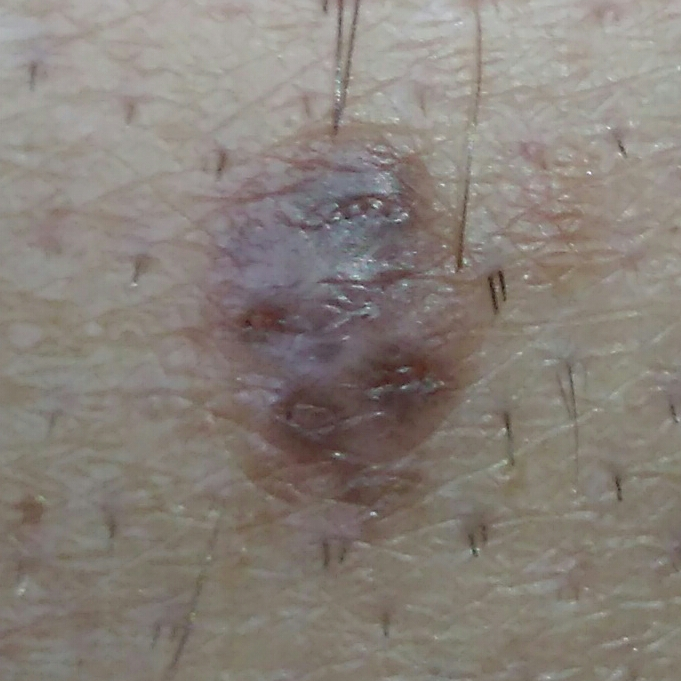  patient:
    age: 27
    gender: male
  risk_factors:
    positive:
      - prior cancer (patient or family)
      - pesticide exposure
  skin_type: III
  lesion_location: a thigh
  symptoms:
    present:
      - growth
      - elevation
    absent:
      - change in appearance
      - pain
  diagnosis:
    name: nevus
    code: NEV
    malignancy: benign
    confirmation: histopathology